A subject in their early 30s — 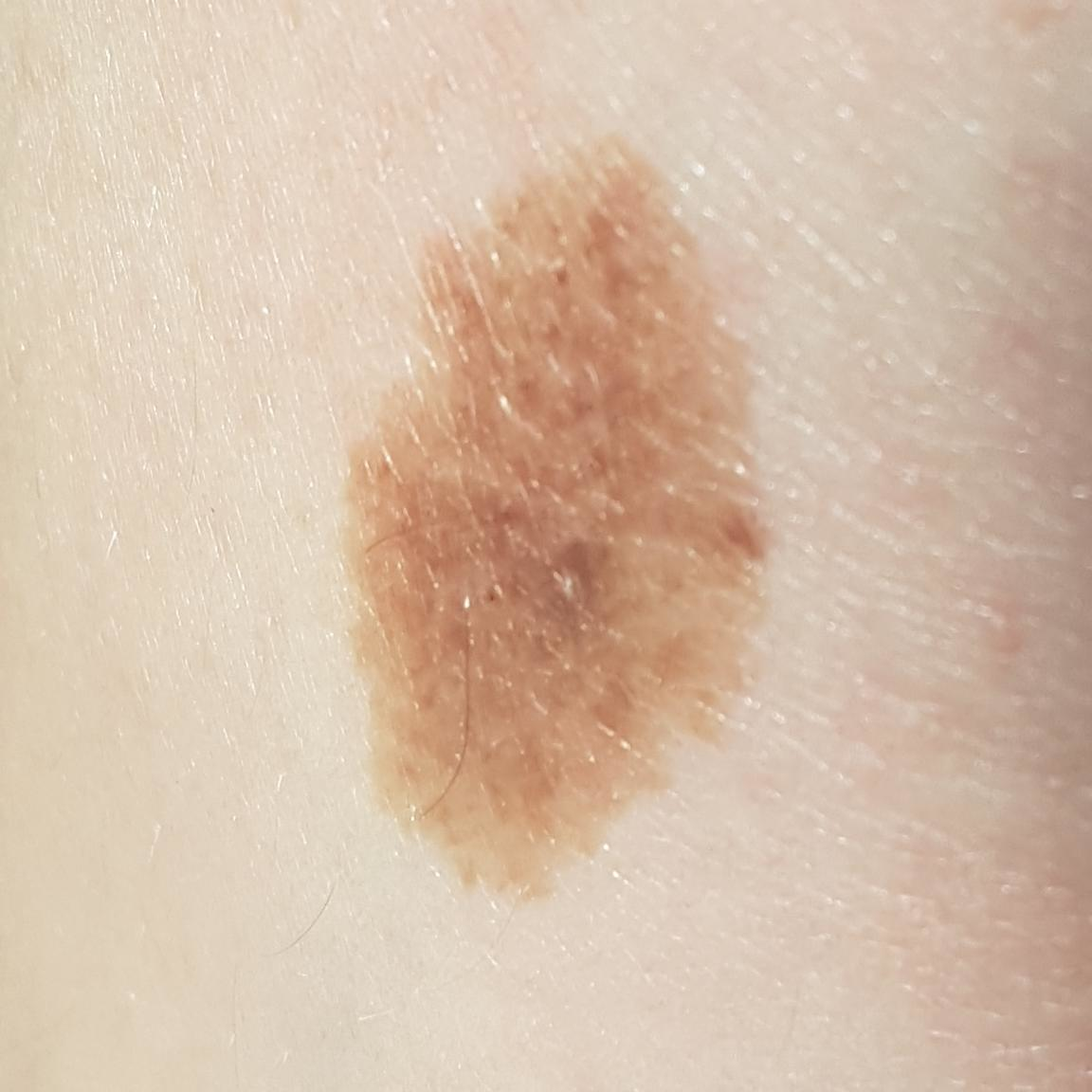<case>
<lesion_location>a thigh</lesion_location>
<diagnosis>
<name>nevus</name>
<code>NEV</code>
<malignancy>benign</malignancy>
<confirmation>clinical consensus</confirmation>
</diagnosis>
</case>